The subject is a male aged approximately 60 · this is a dermoscopic photograph of a skin lesion — 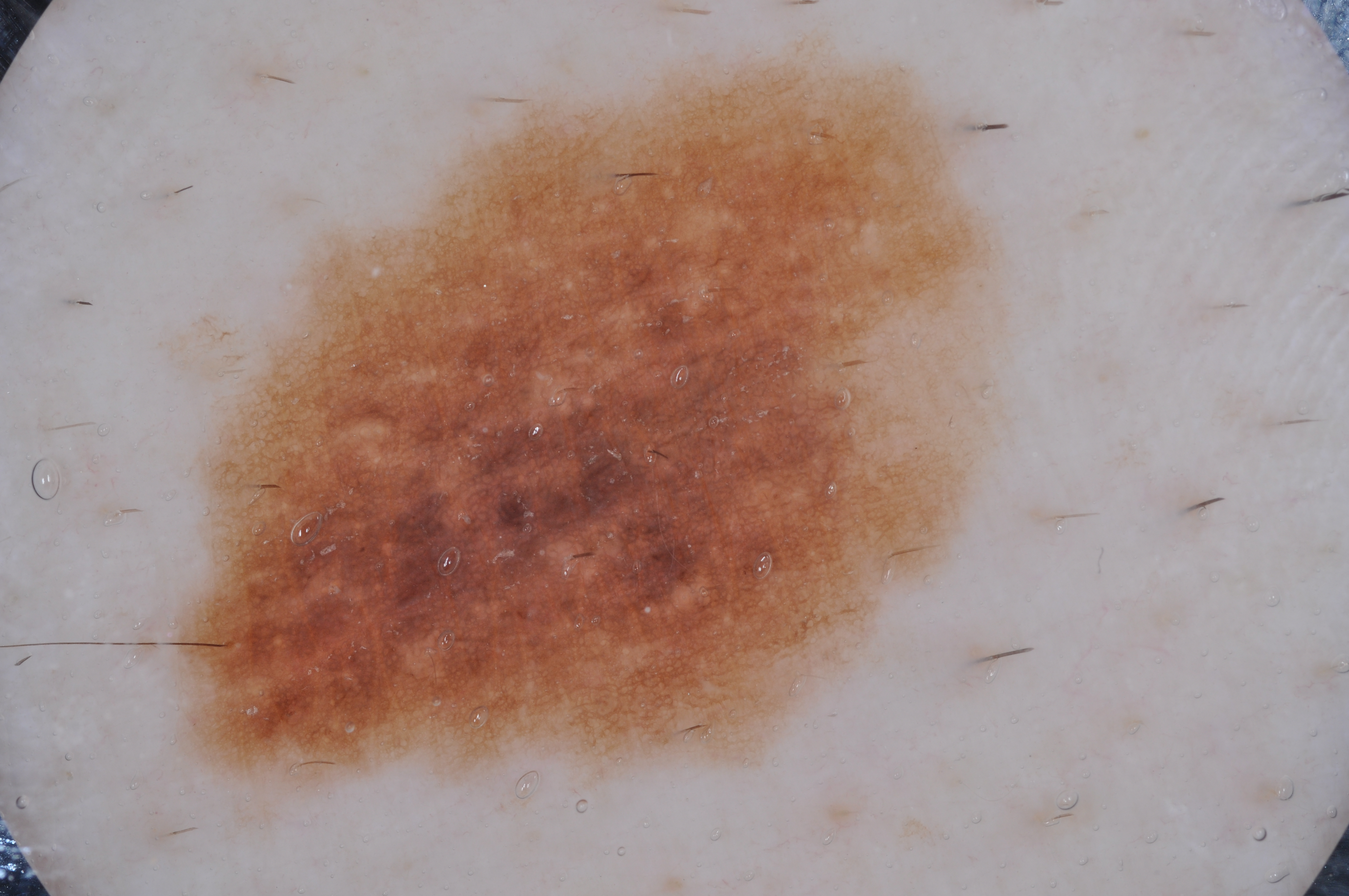Findings:
– location — x1=169 y1=63 x2=991 y2=784
– dermoscopic features — pigment network and milia-like cysts; absent: streaks and negative network
– lesion extent — large
– diagnosis — a melanoma, a malignant lesion